This image was taken at a distance — 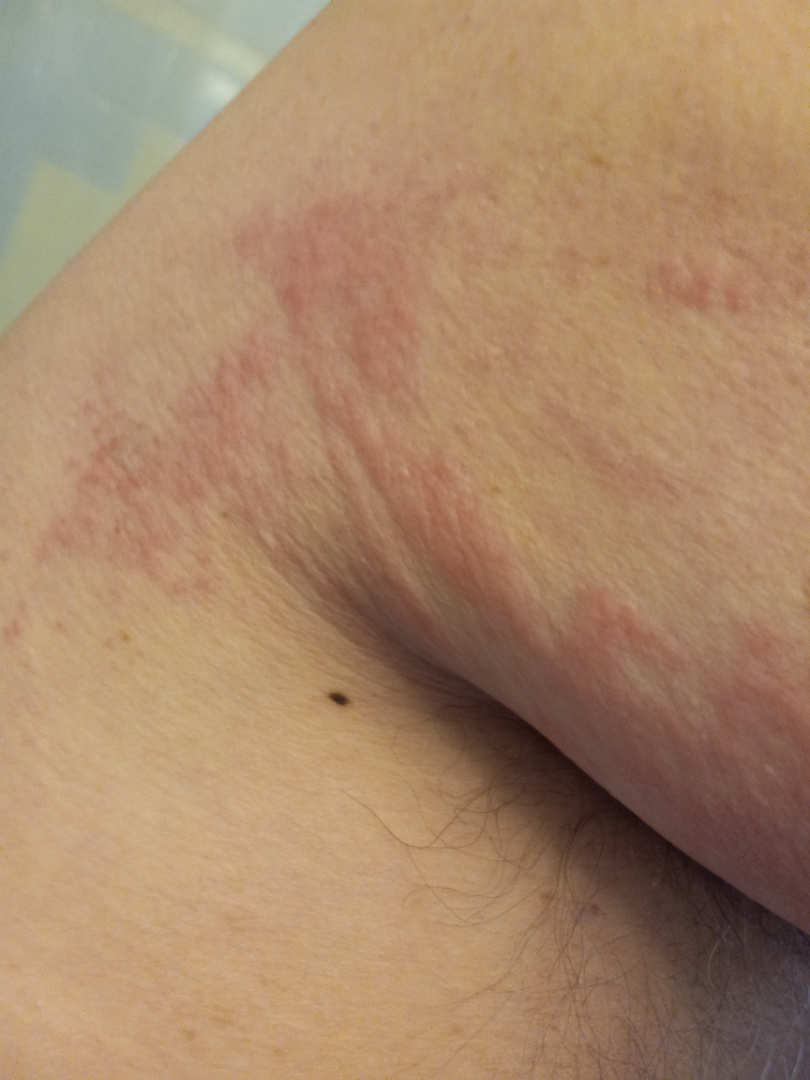The reviewing dermatologist's impression was: most consistent with Urticaria.